A dermatoscopic image of a skin lesion:
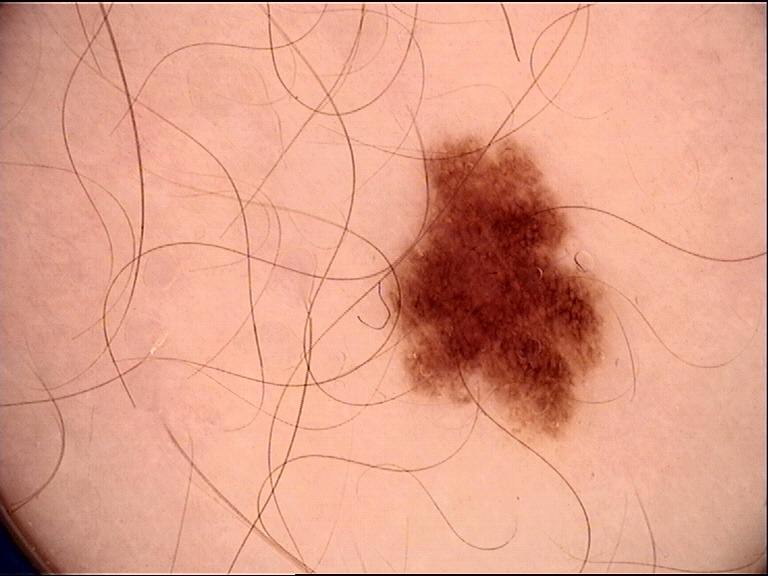Q: What is the diagnosis?
A: junctional nevus (expert consensus)